A dermatoscopic image of a skin lesion: 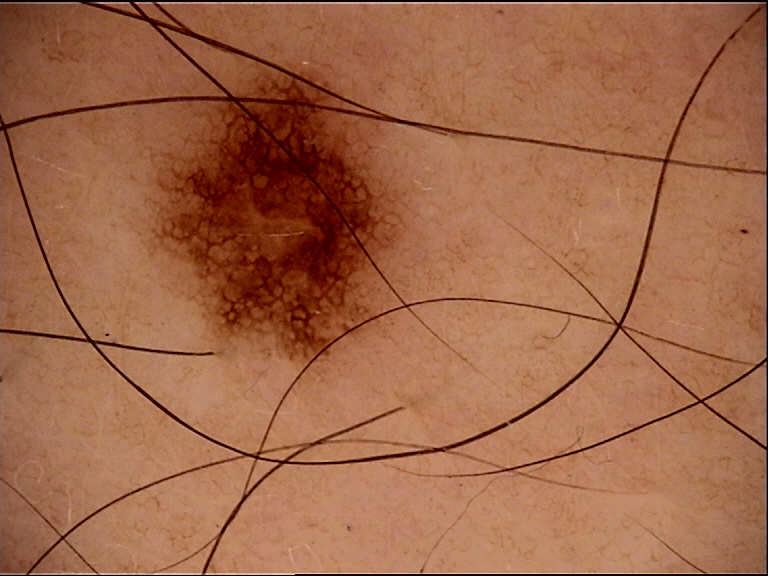{
  "diagnosis": {
    "name": "dysplastic junctional nevus",
    "code": "jd",
    "malignancy": "benign",
    "super_class": "melanocytic",
    "confirmation": "expert consensus"
  }
}